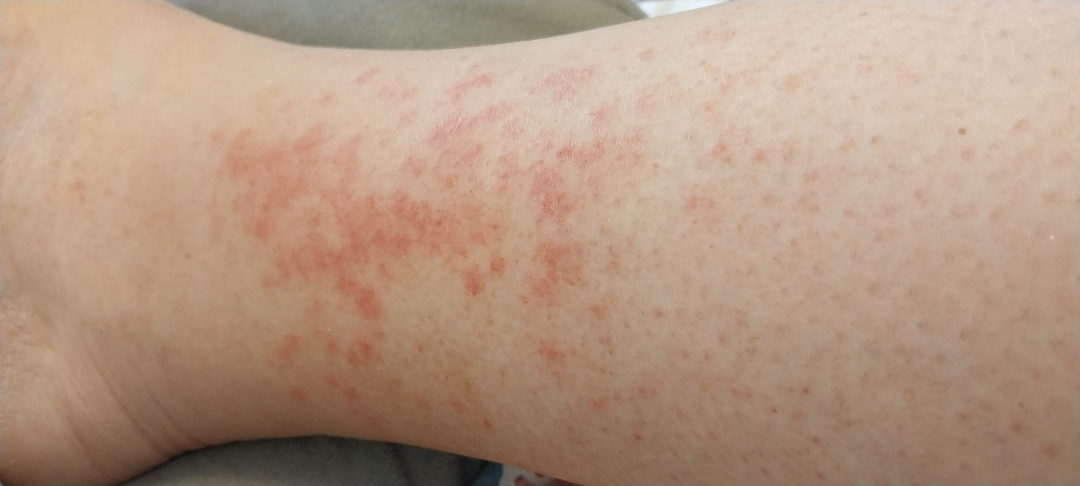{"assessment": "not assessable", "shot_type": "close-up"}